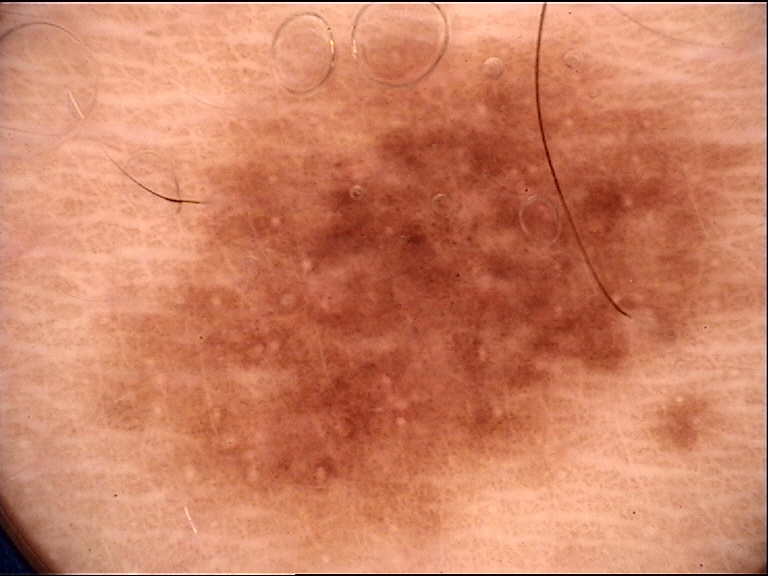A dermoscopic close-up of a skin lesion.
Diagnosed as a dysplastic junctional nevus.